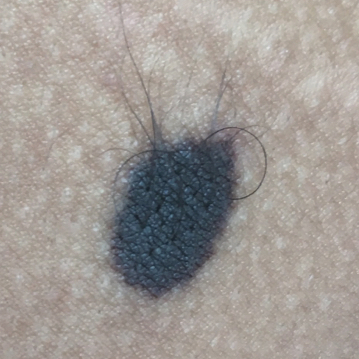A clinical photograph of a skin lesion.
The lesion involves a forearm.
The patient describes that the lesion has not changed and has not bled.
The diagnostic impression was a nevus.